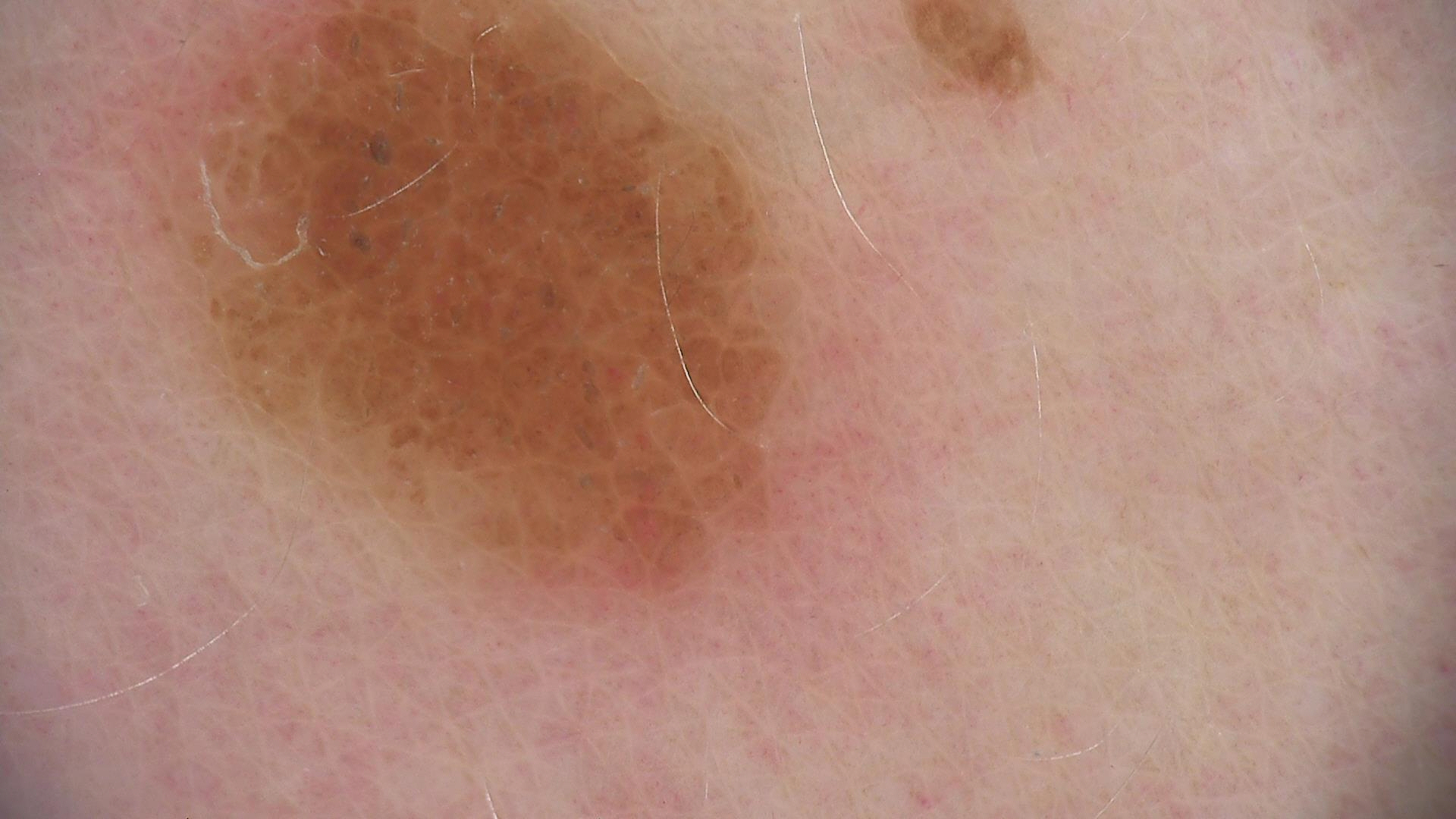Summary:
A dermoscopic close-up of a skin lesion. This is a banal lesion.
Impression:
Labeled as a compound nevus.